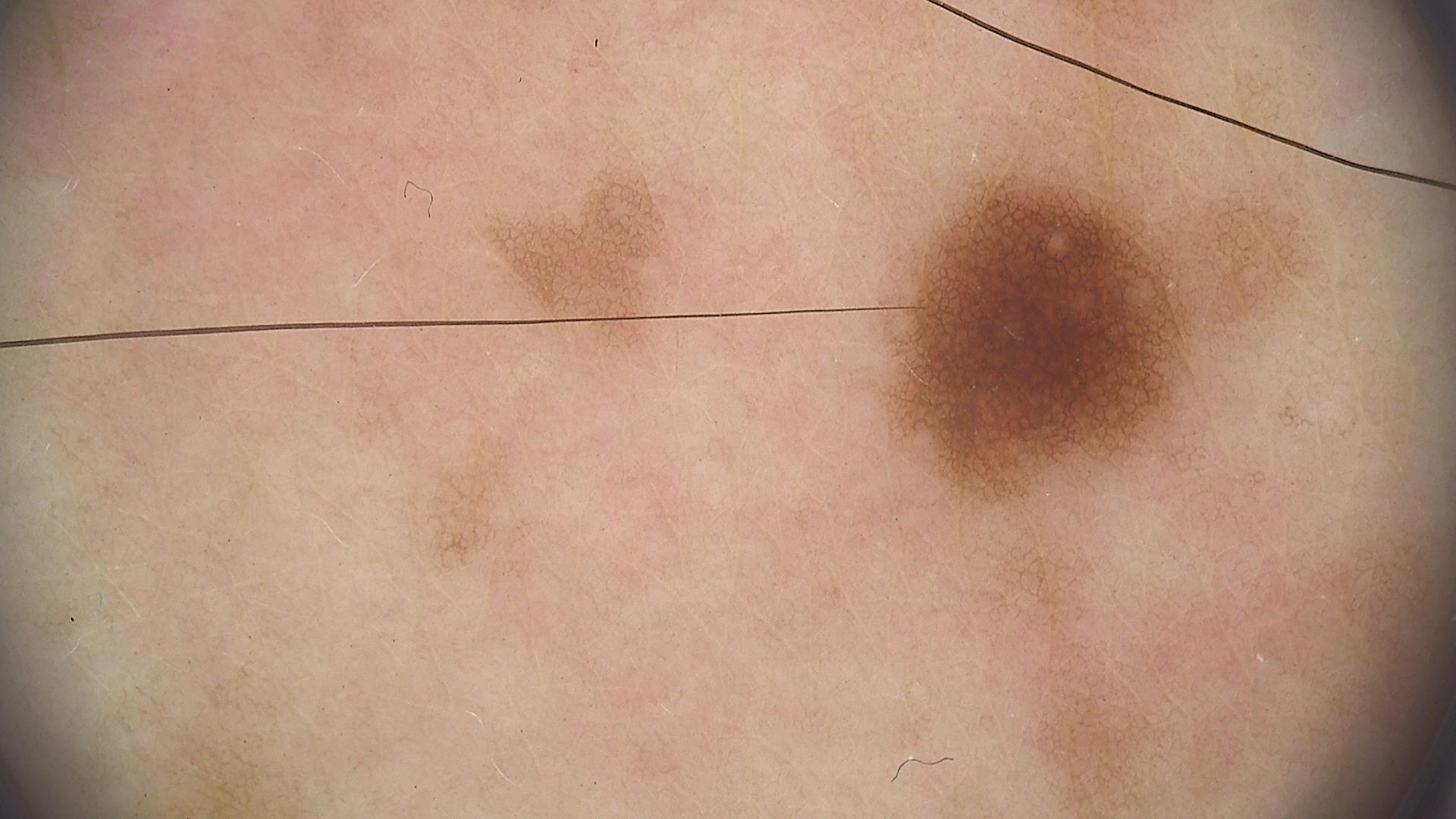- image type: dermoscopy
- class: dysplastic junctional nevus (expert consensus)